Female contributor, age 50–59; close-up view; located on the arm: 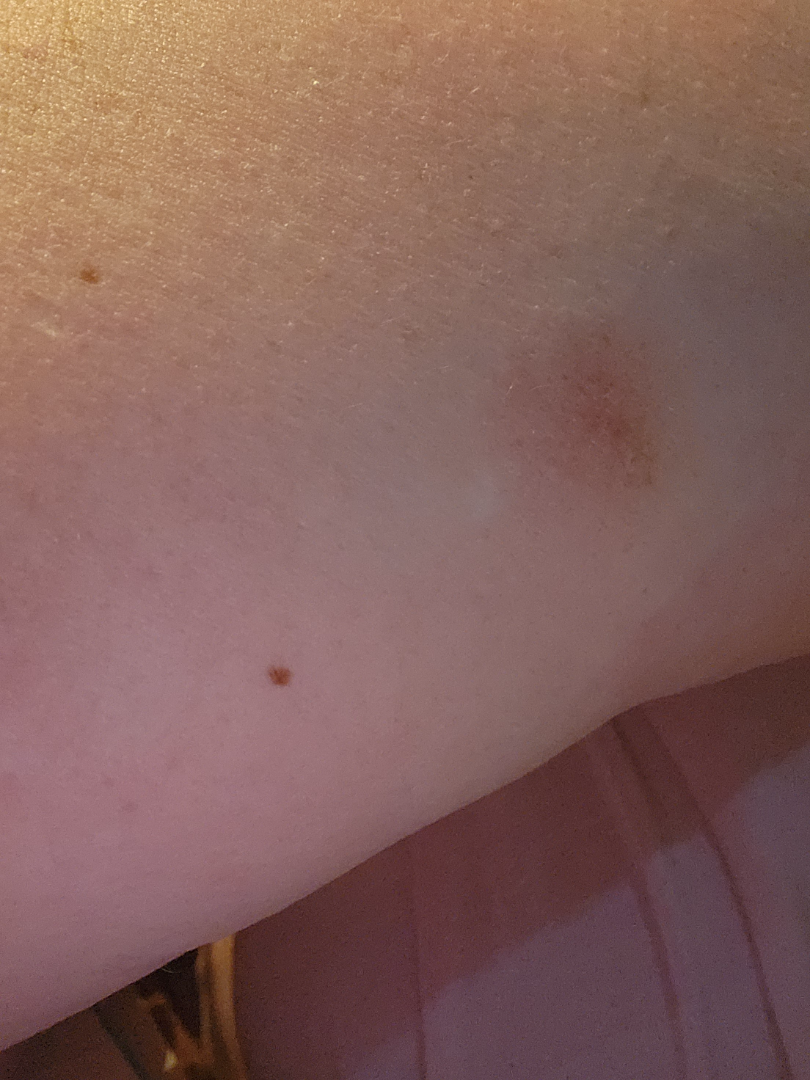assessment: indeterminate